The patient was assessed as skin type II. A male subject approximately 60 years of age. A dermoscopic image of a skin lesion — 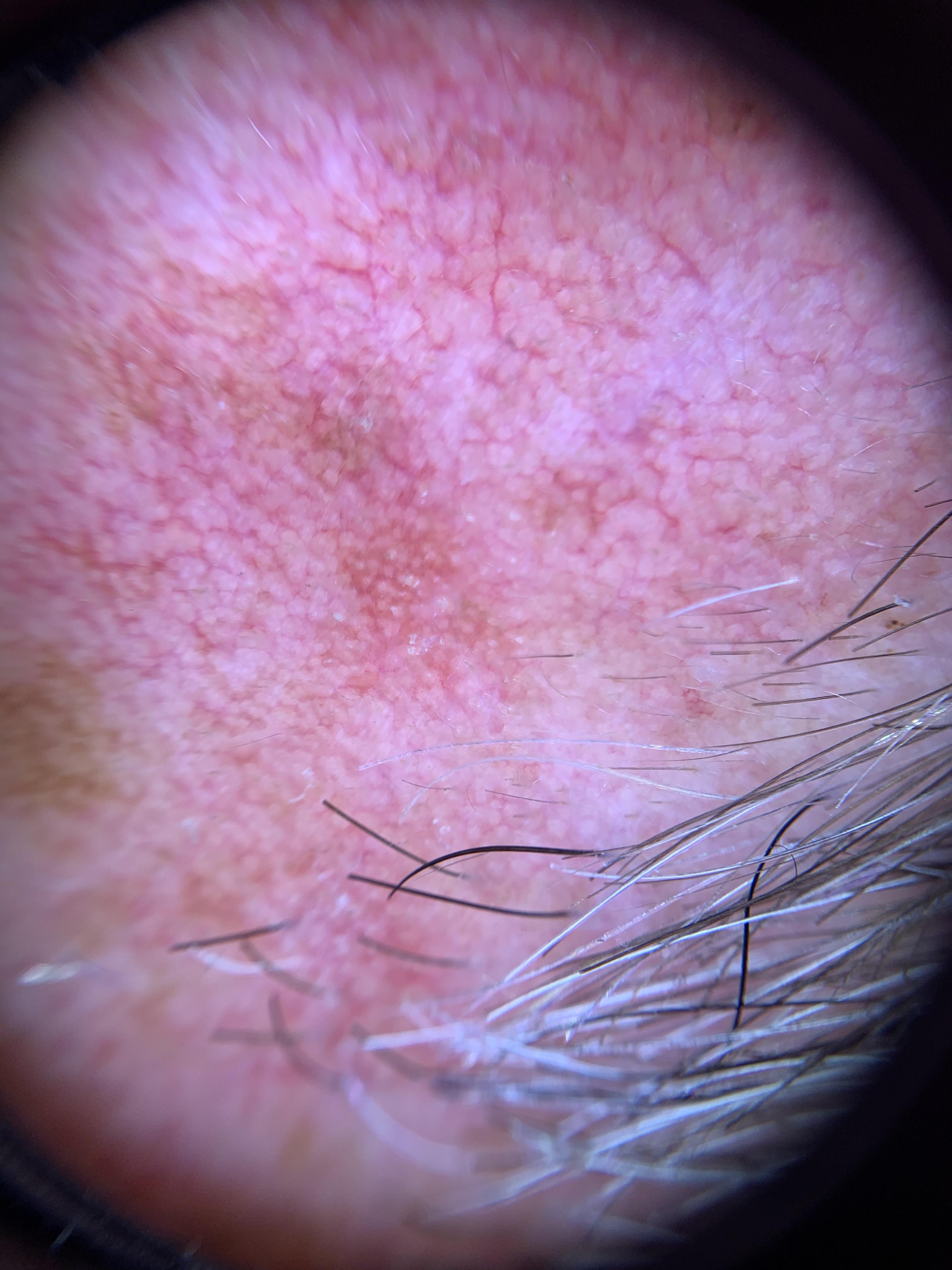anatomic site — the head or neck
diagnostic label — Solar or actinic keratosis (clinical impression)